A dermoscopic image of a skin lesion.
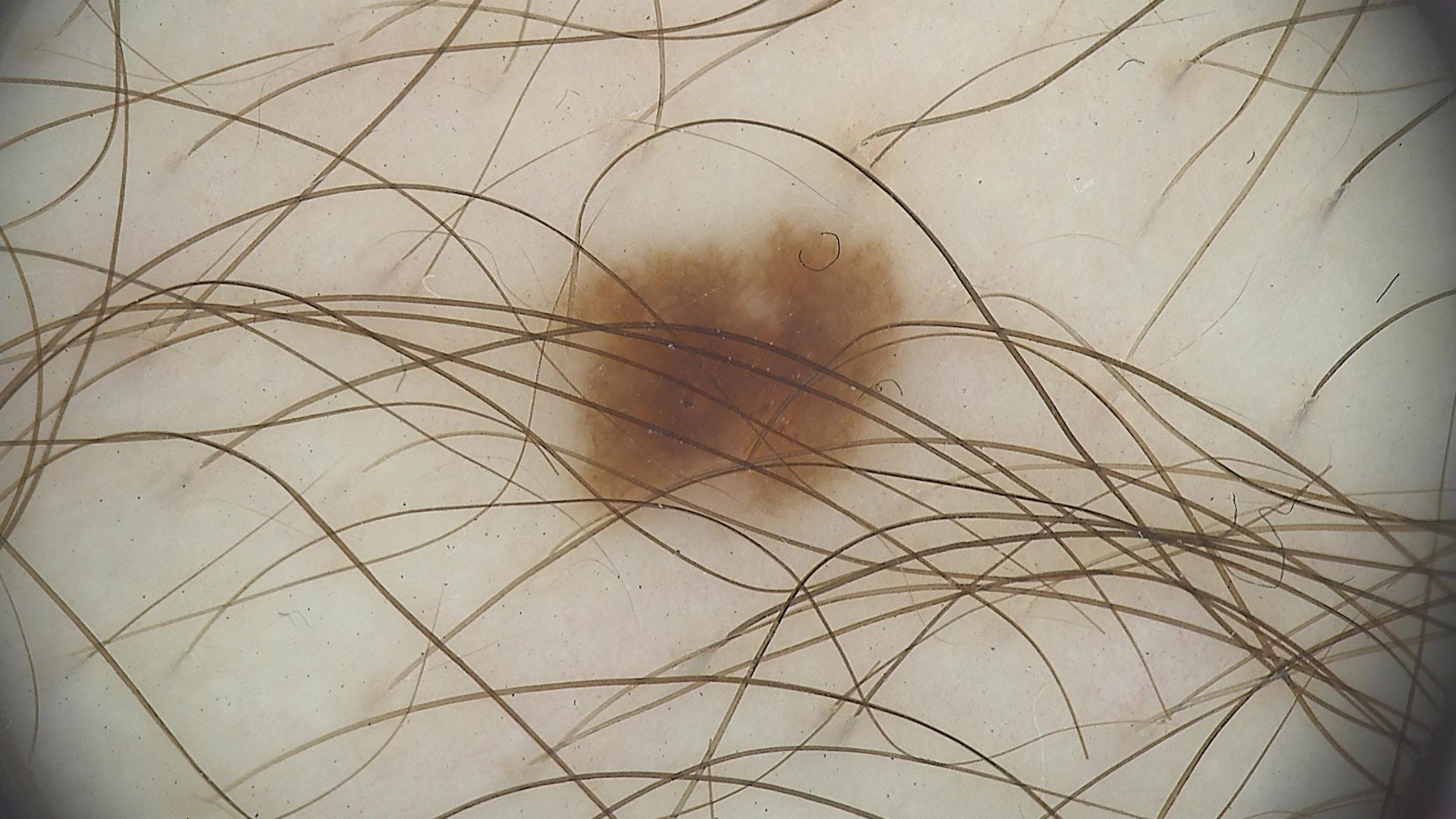{"diagnosis": {"name": "dysplastic junctional nevus", "code": "jd", "malignancy": "benign", "super_class": "melanocytic", "confirmation": "expert consensus"}}